A dermoscopic photograph of a skin lesion.
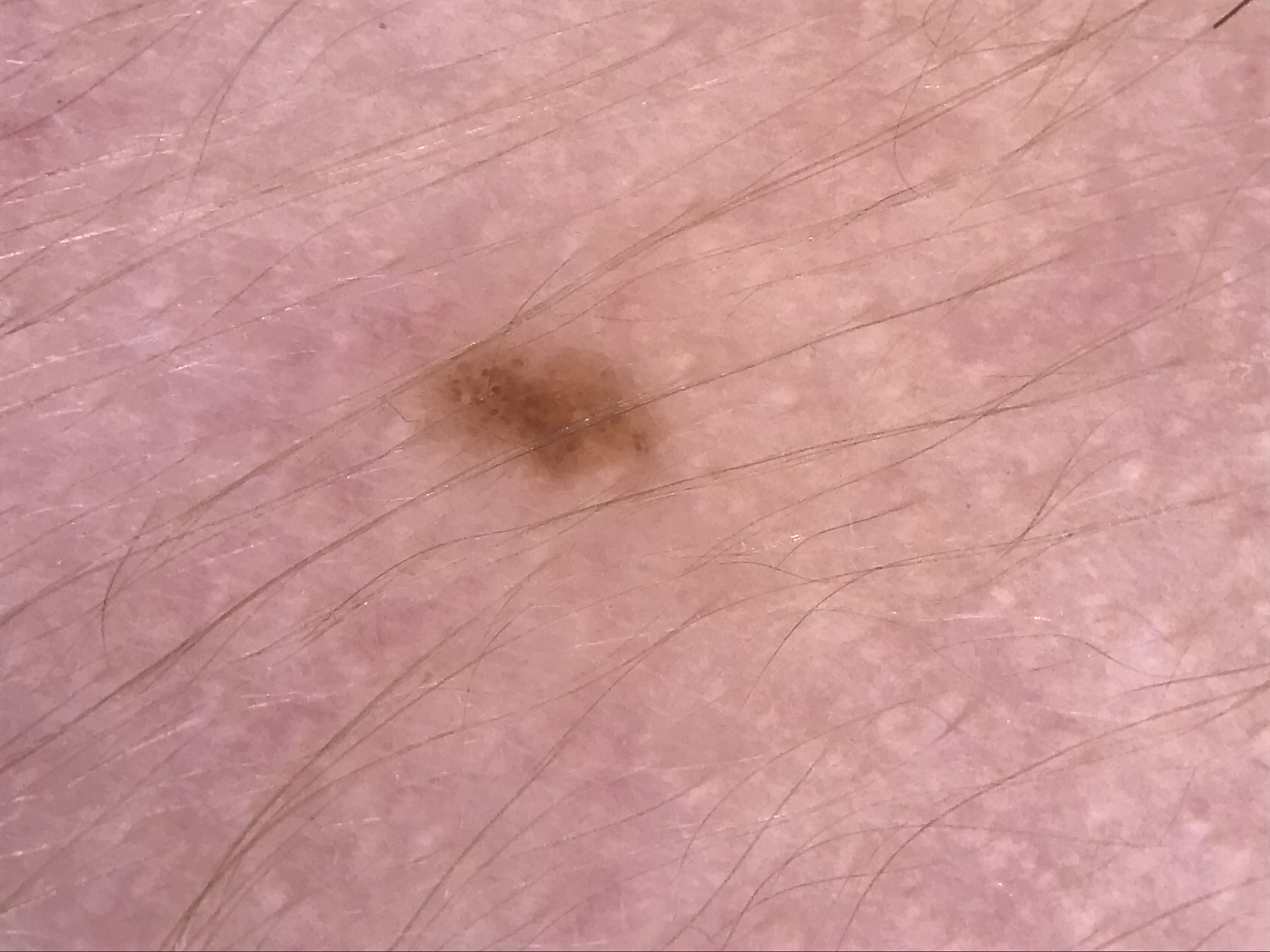Case:
* class · dysplastic junctional nevus (expert consensus)